A dermatoscopic image of a skin lesion:
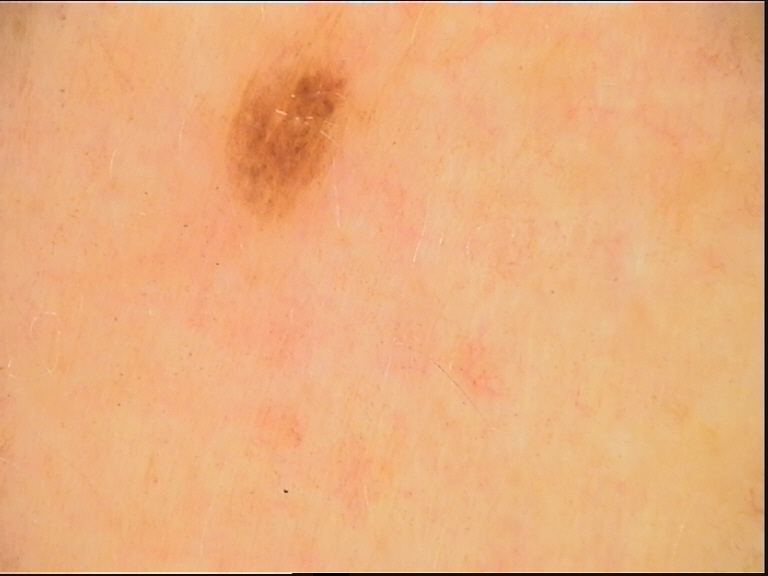  diagnosis:
    name: dysplastic junctional nevus
    code: jd
    malignancy: benign
    super_class: melanocytic
    confirmation: expert consensus